This image was taken at an angle: 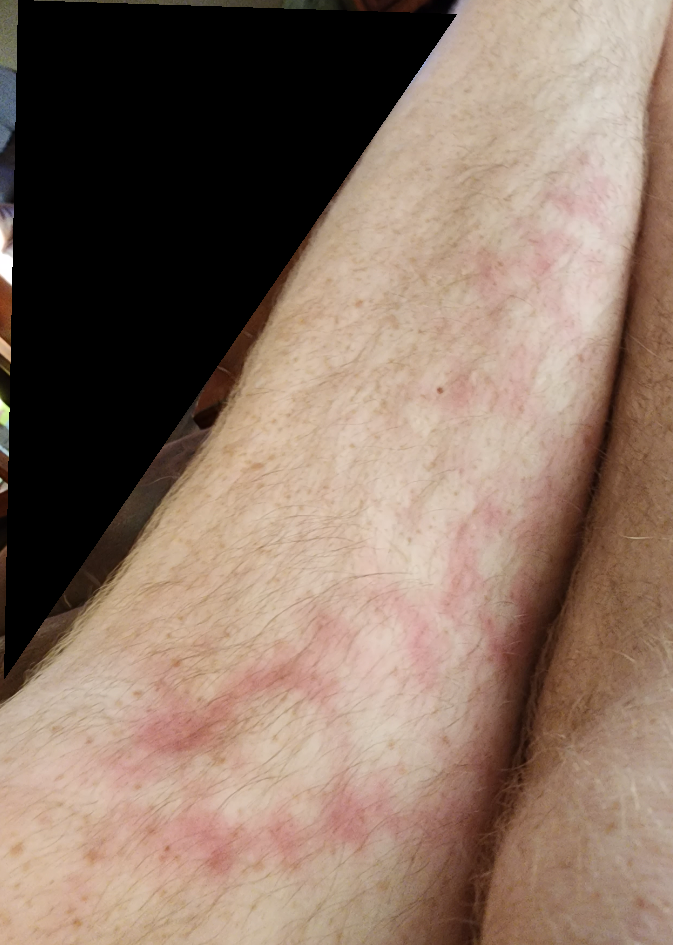<report>
  <differential>
    <tied_lead>Livedo reticularis, Erythema ab igne</tied_lead>
  </differential>
</report>